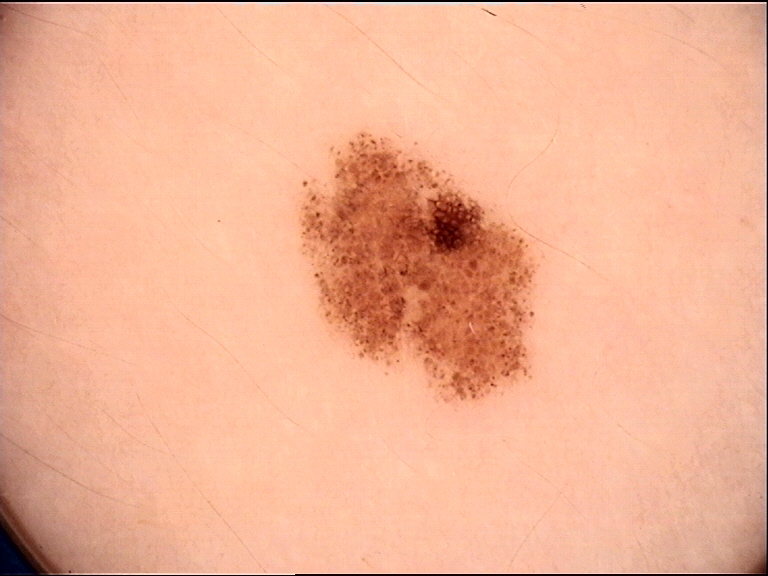diagnostic label — dysplastic junctional nevus (expert consensus)